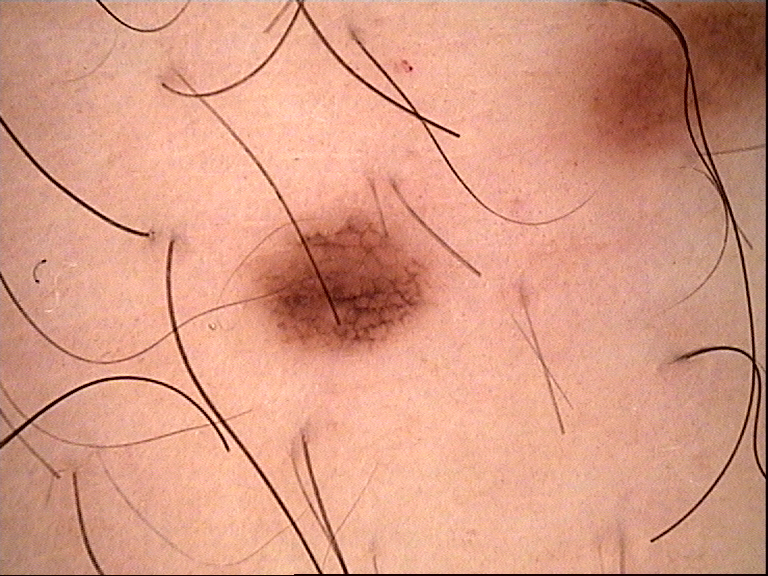Findings: A dermoscopic photograph of a skin lesion. Impression: Classified as a dysplastic junctional nevus.